The lesion involves the arm · reported lesion symptoms include itching · texture is reported as raised or bumpy · the photograph was taken at an angle:
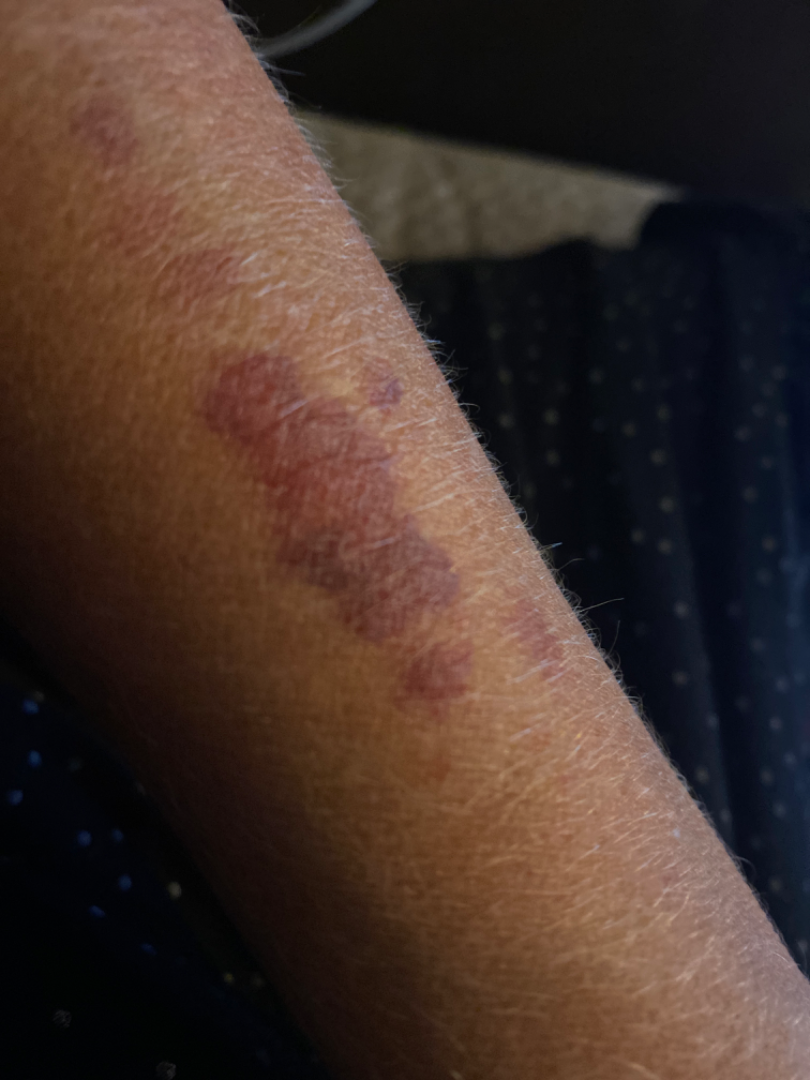Impression: Consistent with ecchymoses.